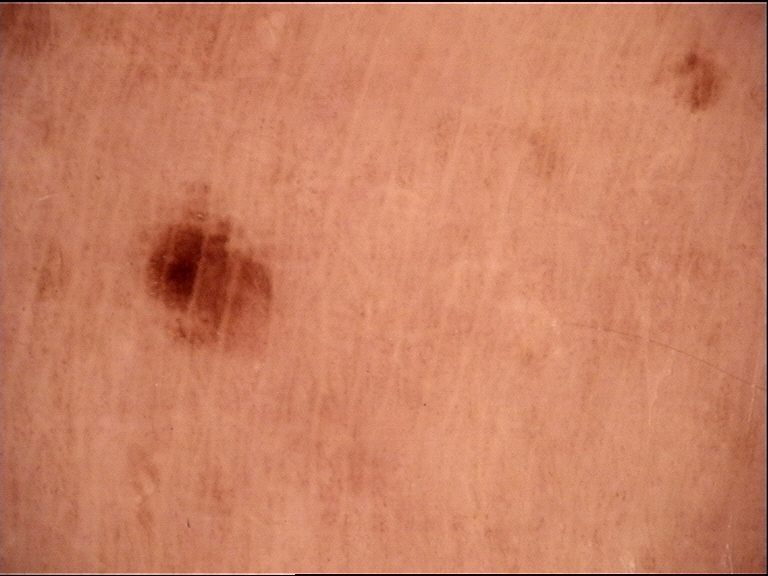{"diagnosis": {"name": "dysplastic junctional nevus", "code": "jd", "malignancy": "benign", "super_class": "melanocytic", "confirmation": "expert consensus"}}